A dermoscopy image of a single skin lesion: 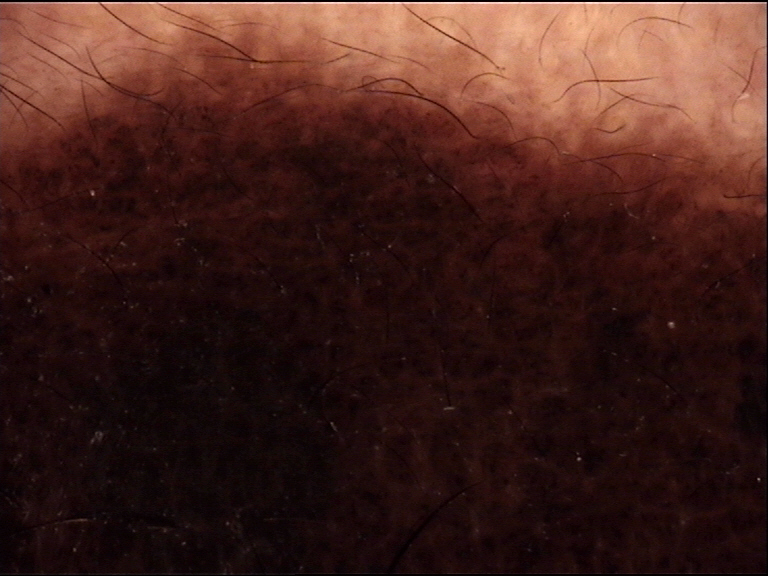assessment: congenital compound nevus (expert consensus)